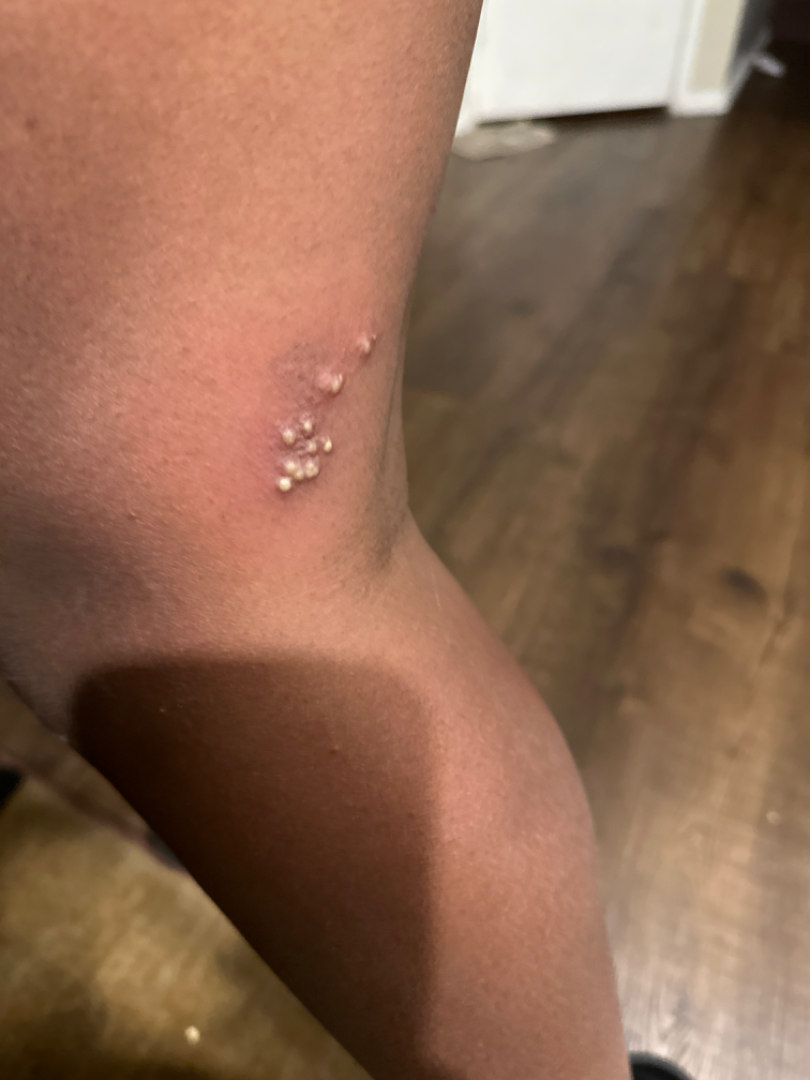<case>
  <shot_type>at a distance</shot_type>
  <differential>
    <leading>Milia</leading>
  </differential>
</case>